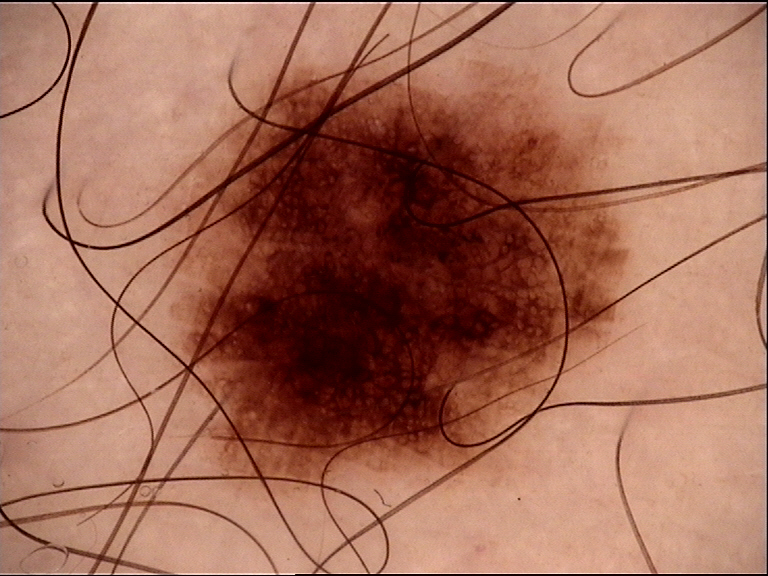A dermoscopic photograph of a skin lesion. The diagnostic label was a dysplastic junctional nevus.